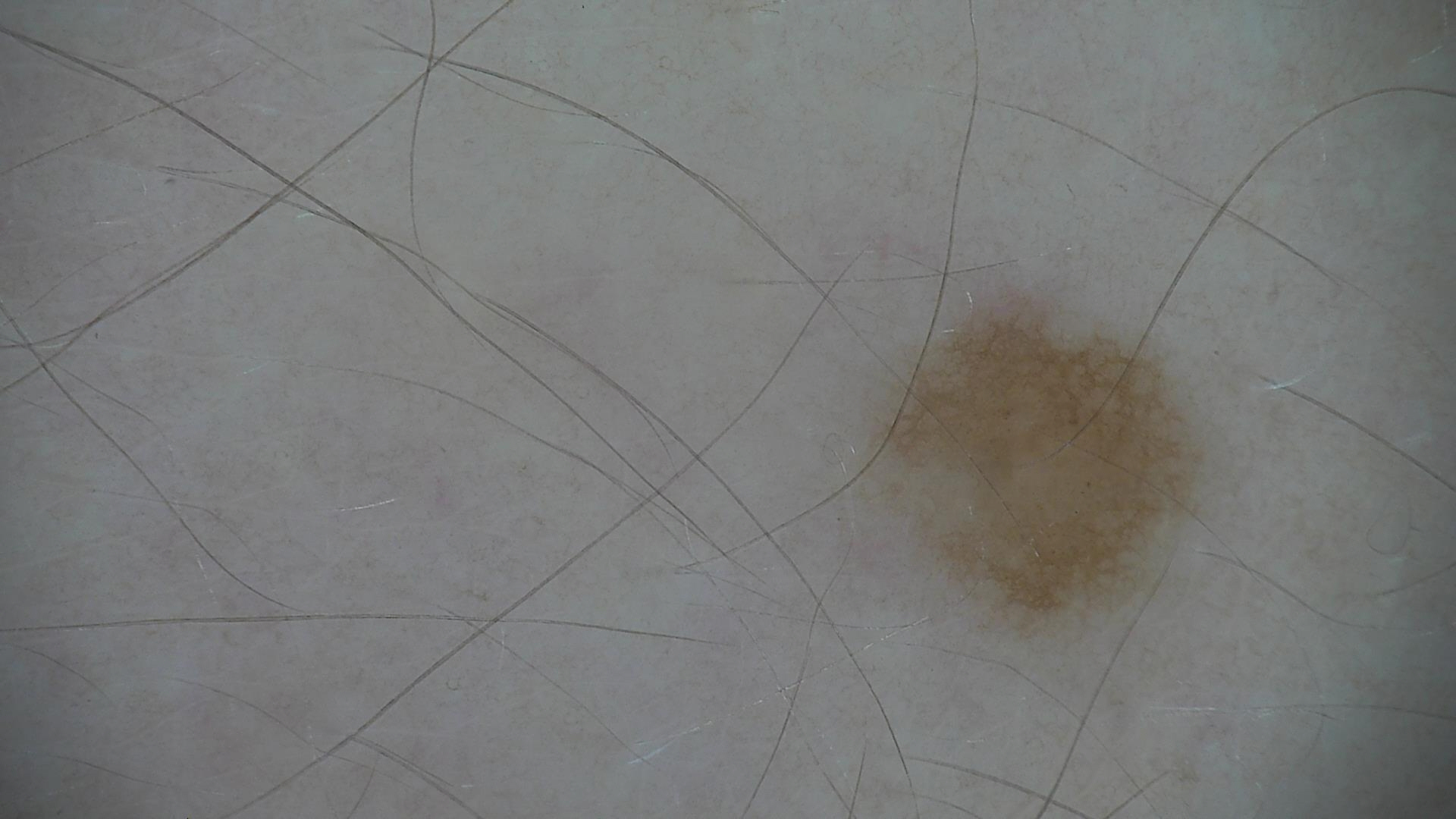label = dysplastic junctional nevus (expert consensus).